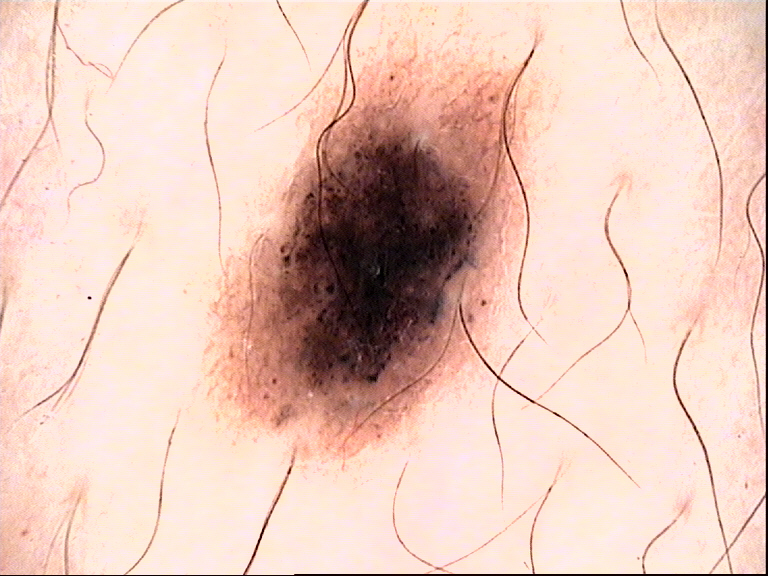Summary: A skin lesion imaged with a dermatoscope. Impression: Classified as a benign lesion — a dysplastic compound nevus.